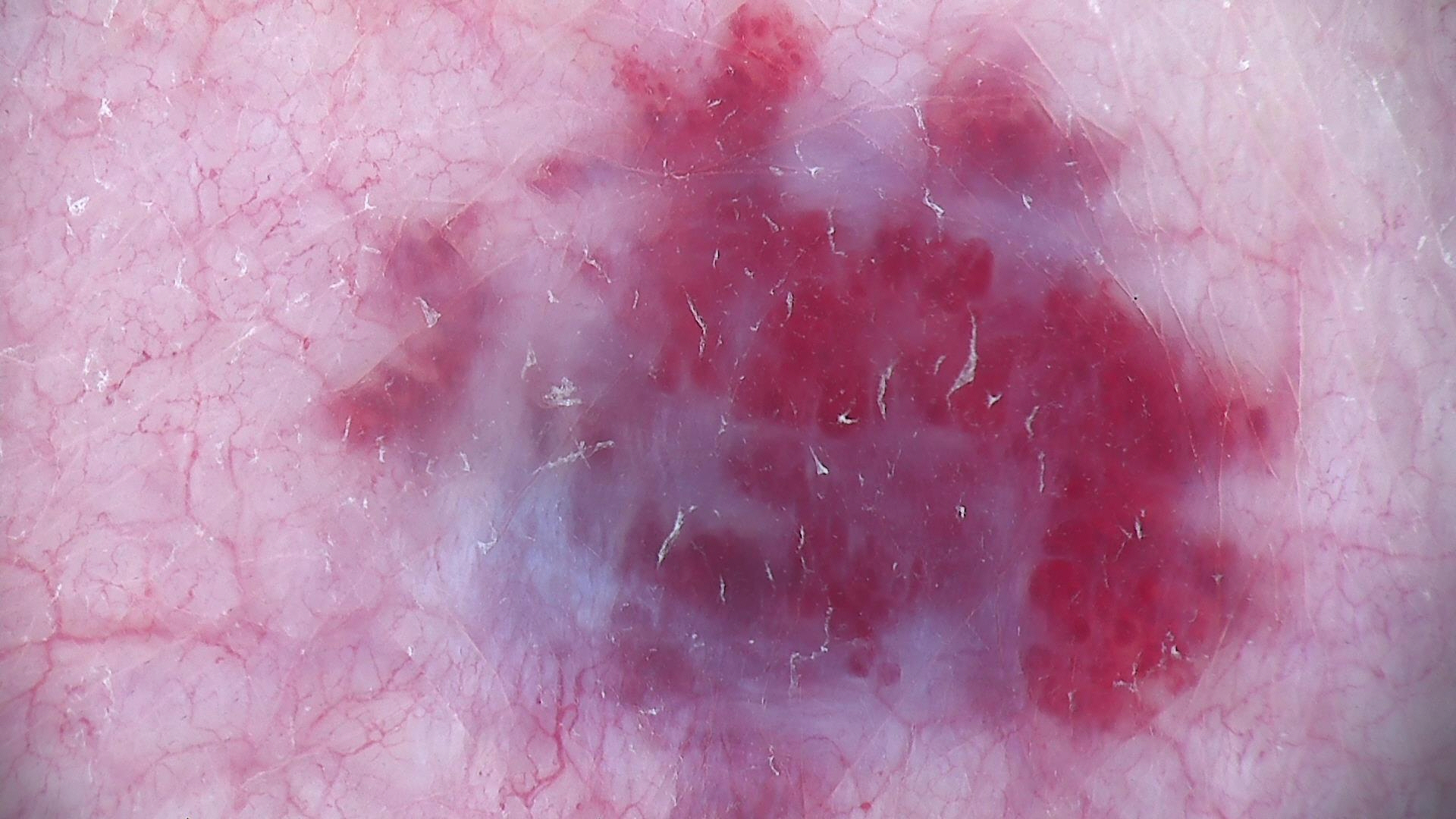Findings:
• diagnostic label — hemangioma (expert consensus)